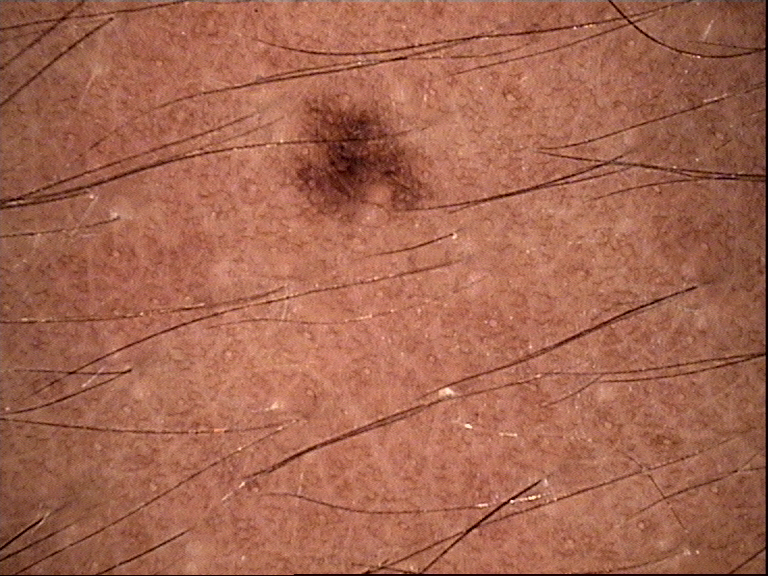image = dermoscopy; diagnostic label = dysplastic junctional nevus (expert consensus).